The arm, back of the hand, front of the torso and back of the torso are involved · present for one to four weeks · the photo was captured at an angle · self-categorized by the patient as a rash — 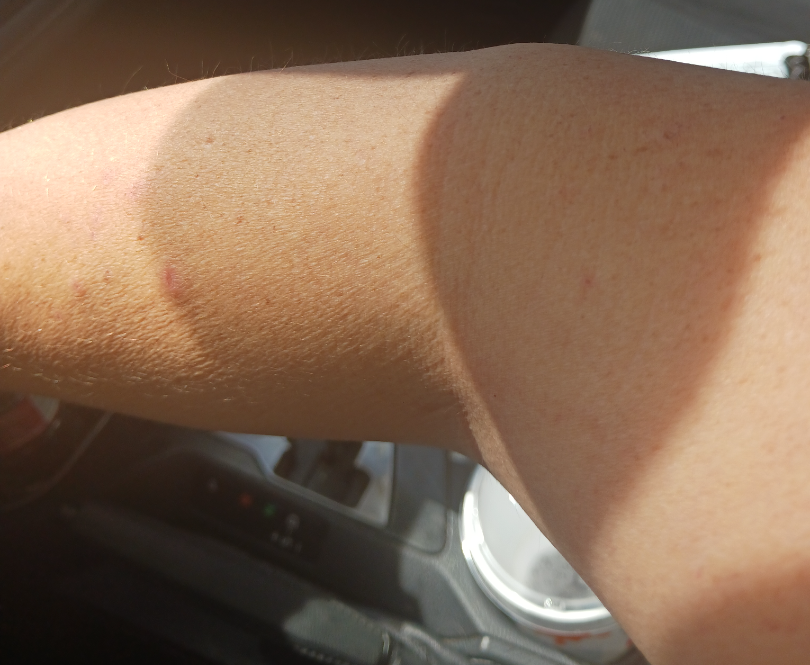Review: The condition could not be reliably identified from the image.